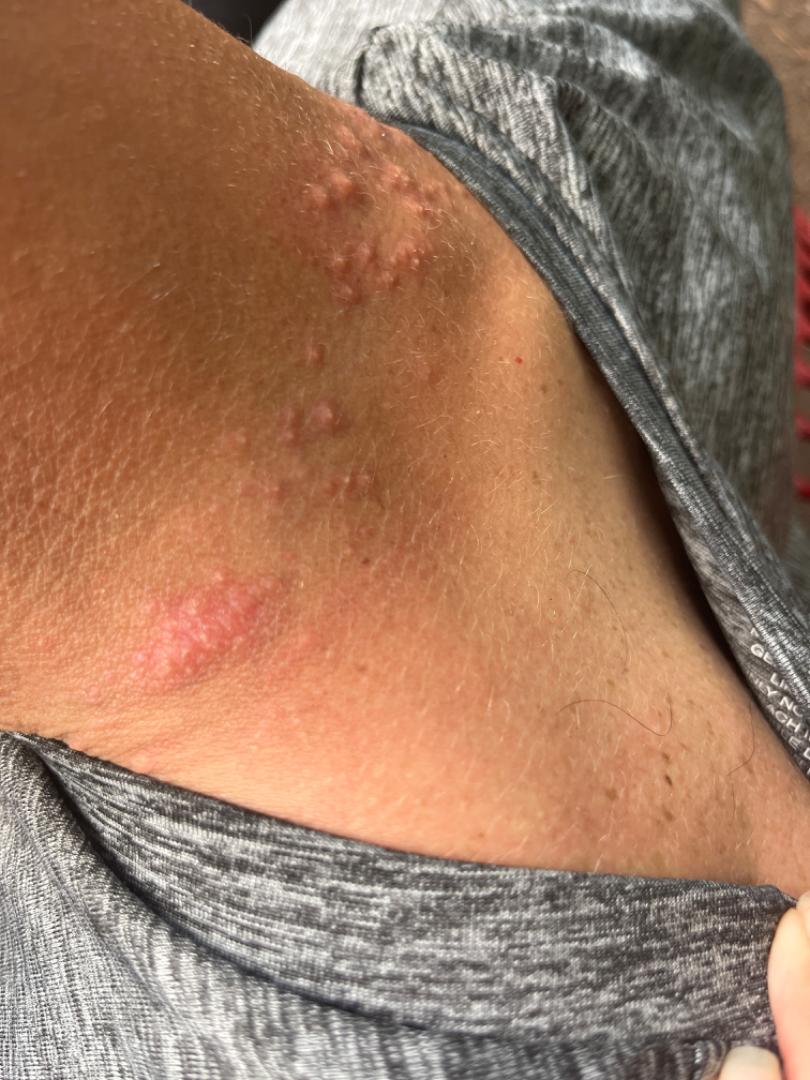The patient described the issue as a rash. An image taken at an angle. The contributor reports the lesion is raised or bumpy. Symptoms reported: itching. The affected area is the head or neck. The condition has been present for one to four weeks. Consistent with Folliculitis.